A female subject, aged around 65 · a dermatoscopic image of a skin lesion:
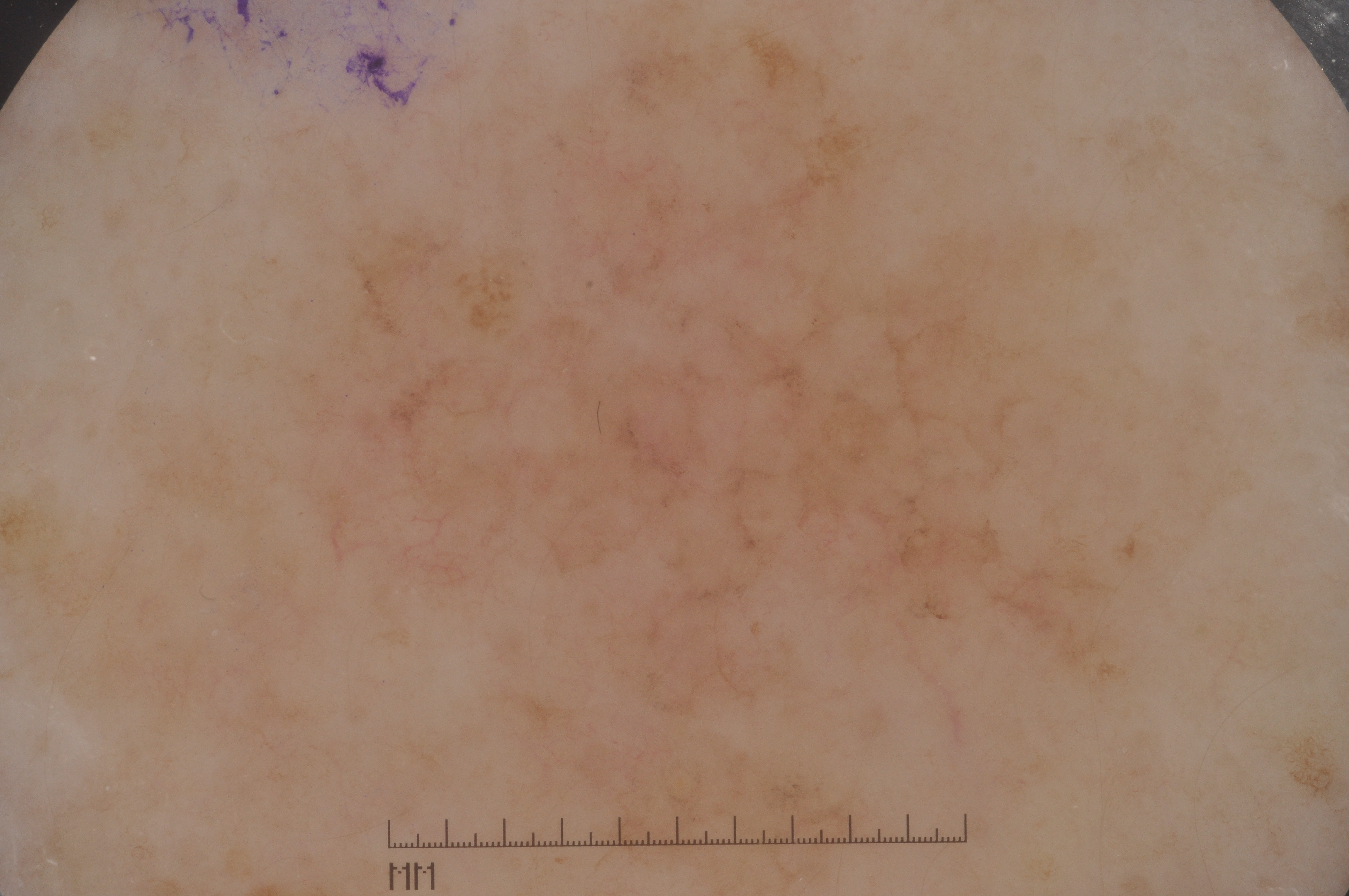The visible lesion spans [184, 9, 1241, 890].
The lesion takes up a large portion of the image.
Dermoscopically, the lesion shows no negative network, milia-like cysts, pigment network, or streaks.
Histopathologically confirmed as a melanoma, a malignant skin lesion.